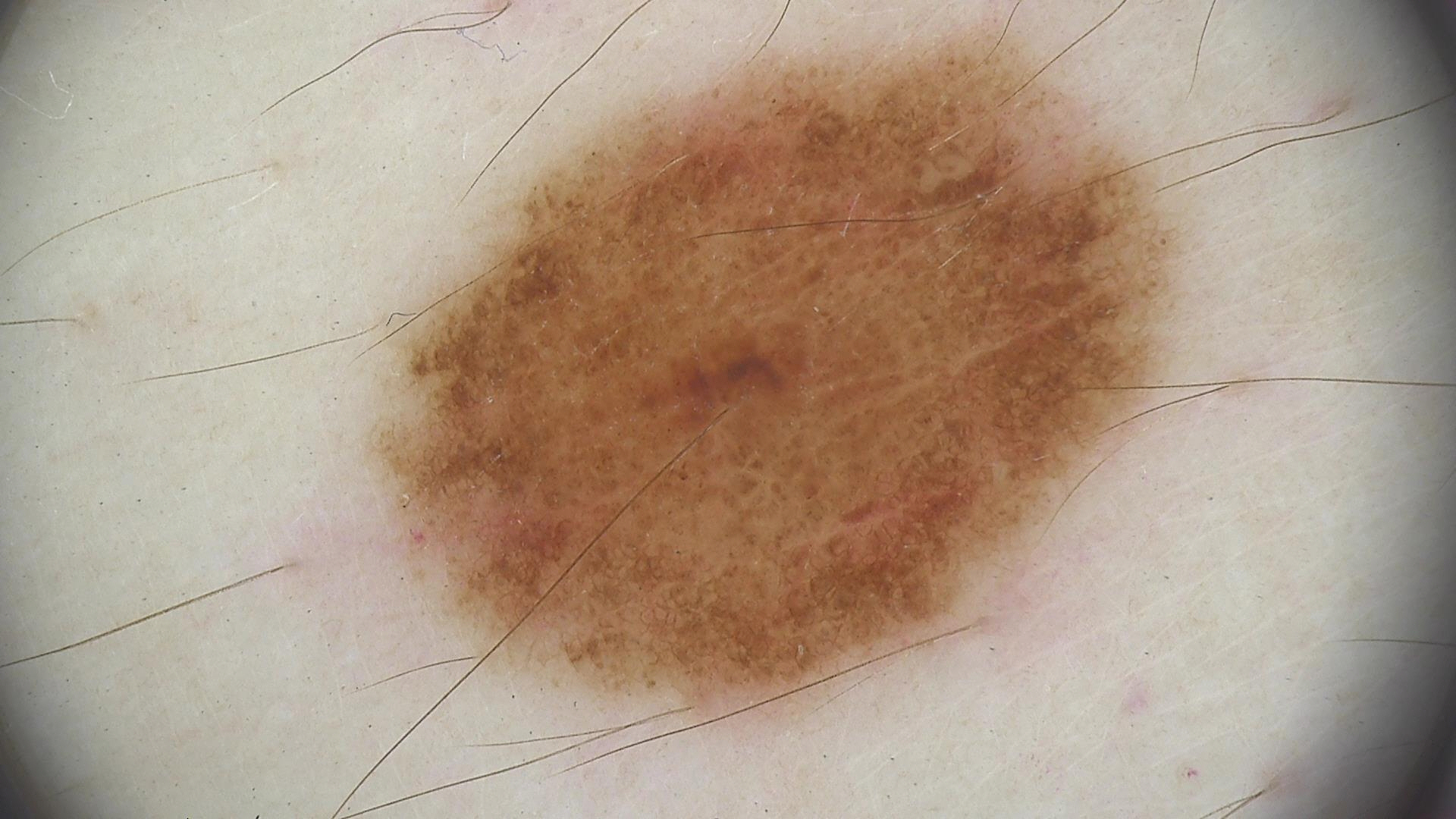Findings: A dermatoscopic image of a skin lesion. Conclusion: The diagnosis was a benign lesion — a dysplastic junctional nevus.